Texture is reported as raised or bumpy; located on the leg, sole of the foot, arm and palm; this image was taken at a distance; reported duration is about one day; the patient indicates associated fatigue; the patient is a female aged 18–29.
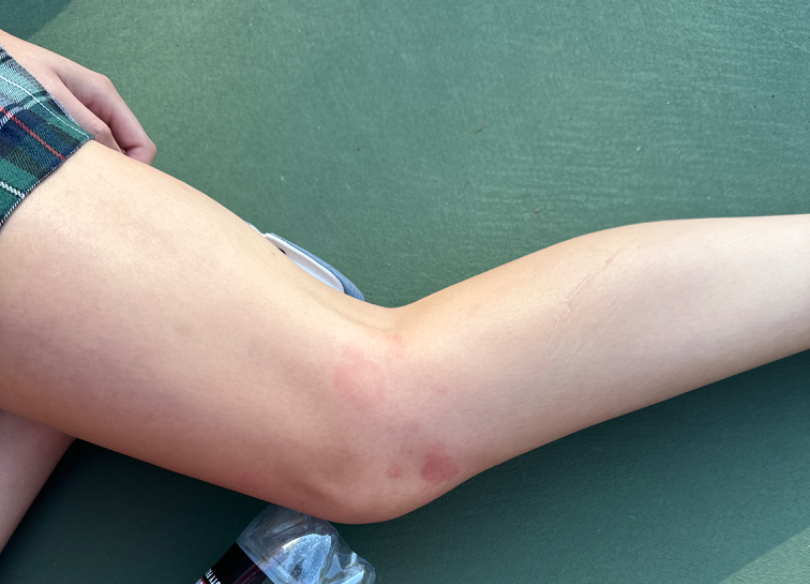Impression:
On teledermatology review, the primary impression is Urticaria; an alternative is Eczema; possibly Granuloma annulare.